A skin lesion imaged with a dermatoscope.
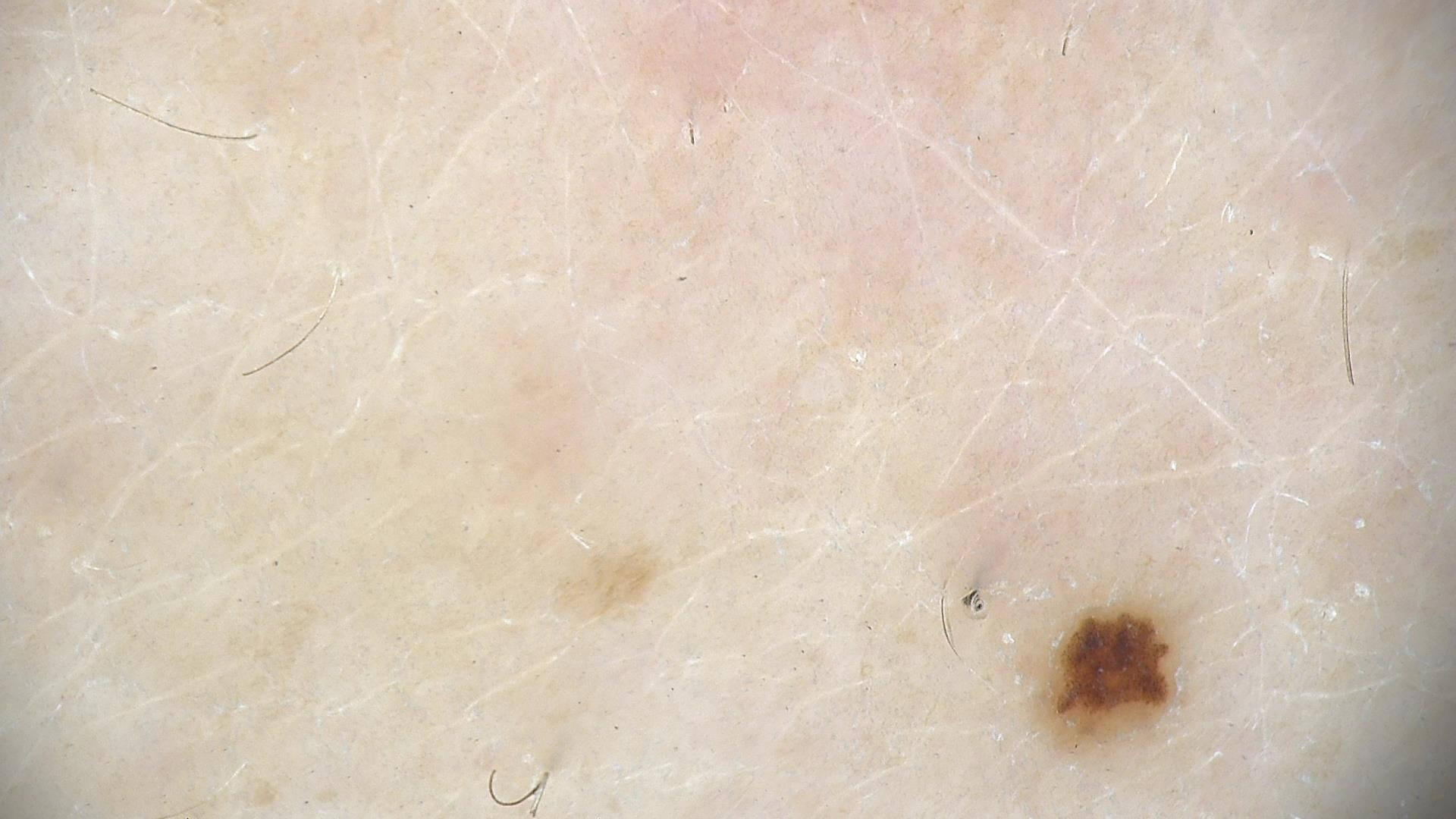The diagnostic label was a dysplastic junctional nevus.